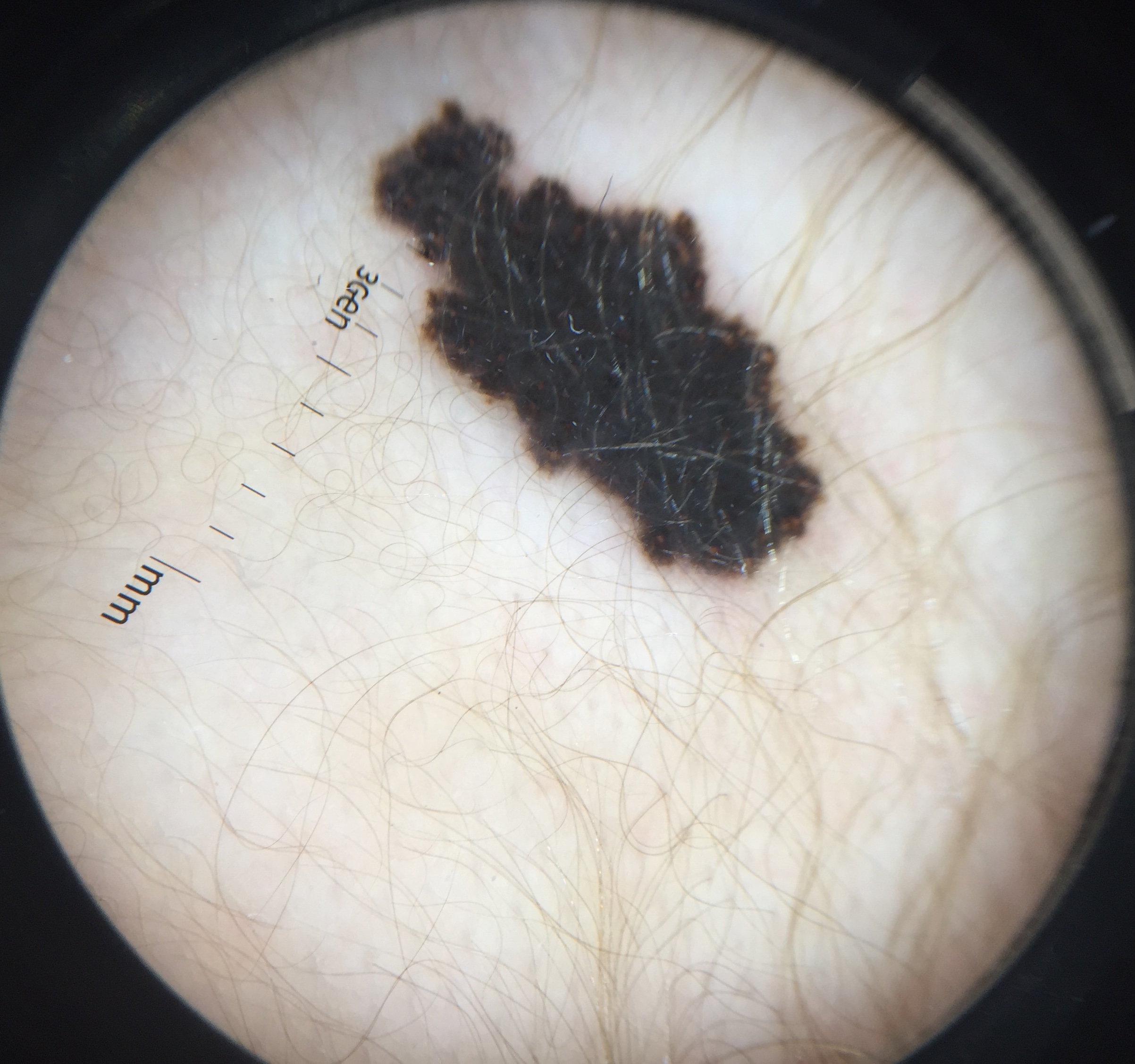Case:
- modality · dermoscopy
- classification · banal
- diagnostic label · congenital compound nevus (expert consensus)